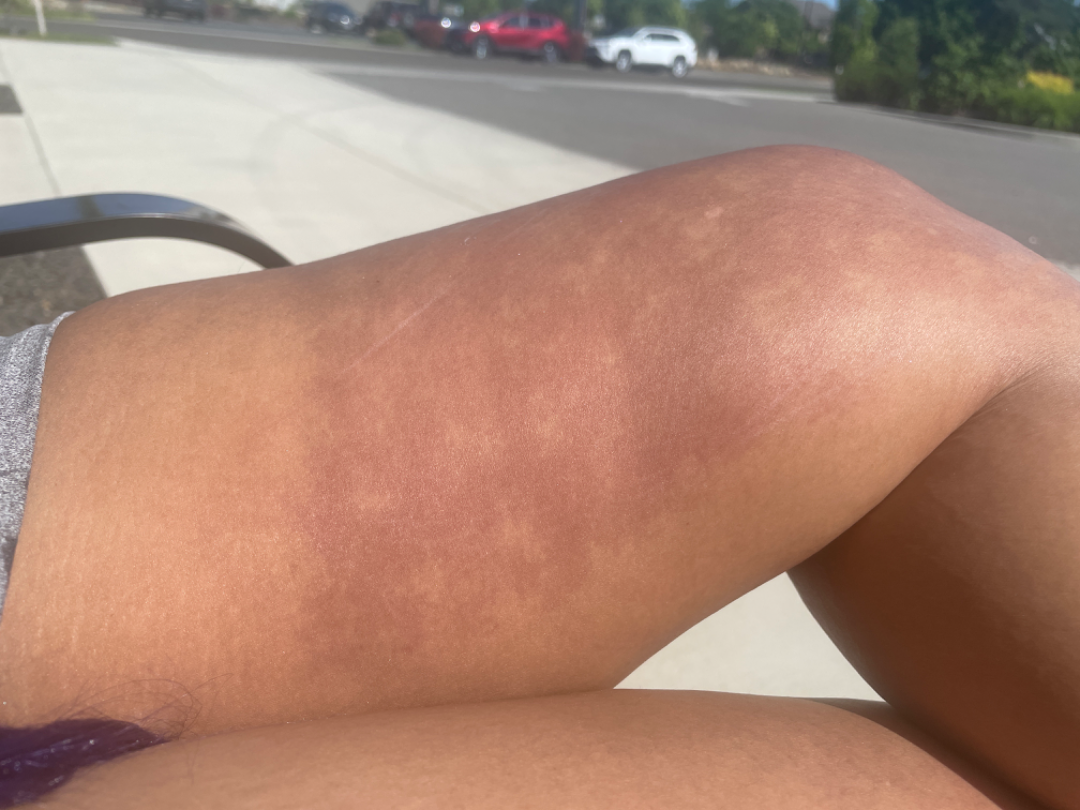<case>
<shot_type>at an angle</shot_type>
<systemic_symptoms>none reported</systemic_symptoms>
<duration>about one day</duration>
<symptoms>burning</symptoms>
<skin_tone>
  <fitzpatrick>IV</fitzpatrick>
</skin_tone>
<body_site>leg</body_site>
<texture>flat</texture>
<differential>
  <leading>Post-Inflammatory hyperpigmentation</leading>
  <considered>Erythema ab igne</considered>
  <unlikely>Erythema dyschromicum perstans</unlikely>
</differential>
</case>